A male subject about 70 years old; a skin lesion imaged with a dermatoscope.
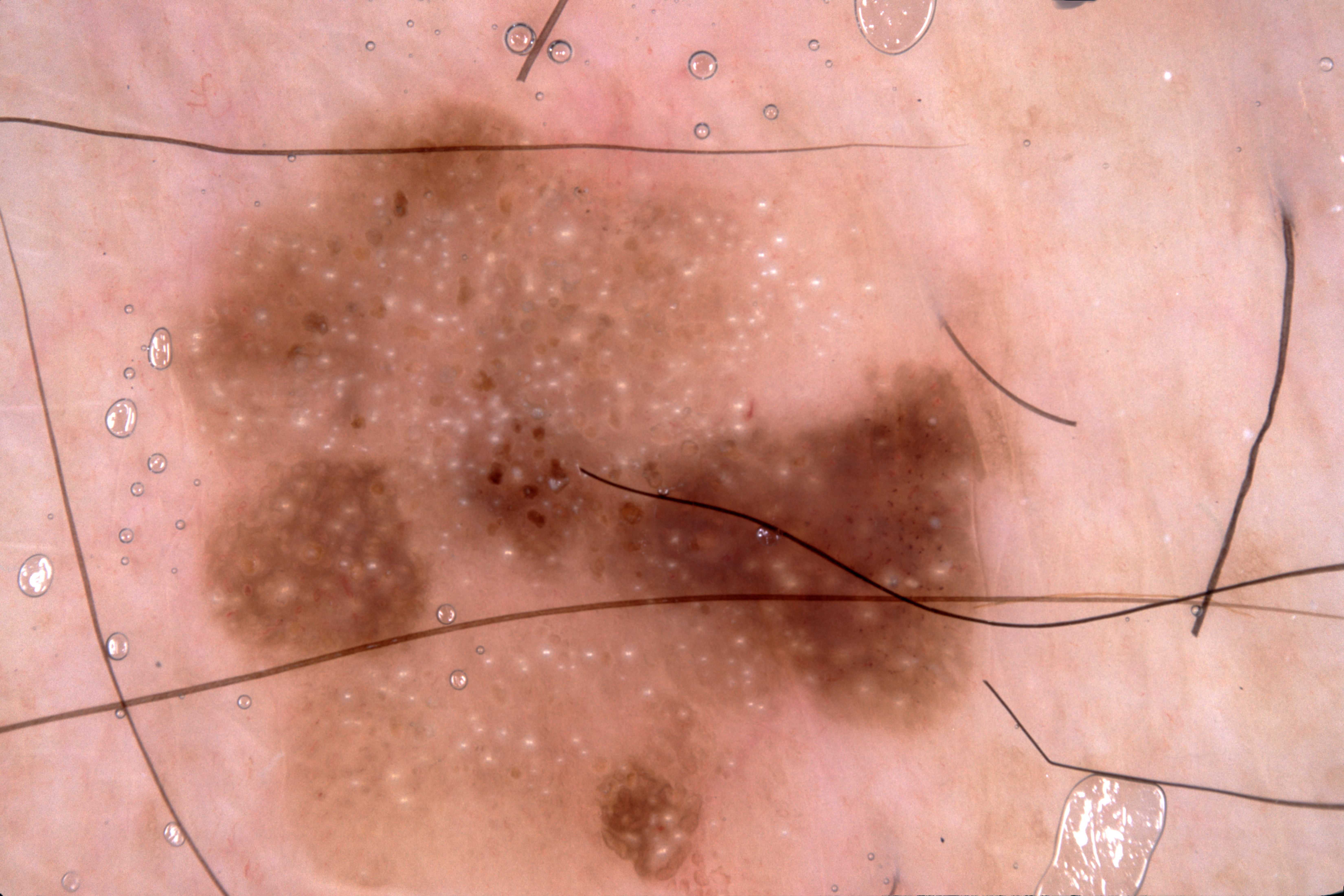Findings:
The lesion spans bbox(168, 91, 1018, 895). The lesion takes up a large portion of the image. The dermoscopic pattern shows milia-like cysts; no pigment network, streaks, or negative network.
Impression:
The diagnostic assessment was a seborrheic keratosis, a benign lesion.